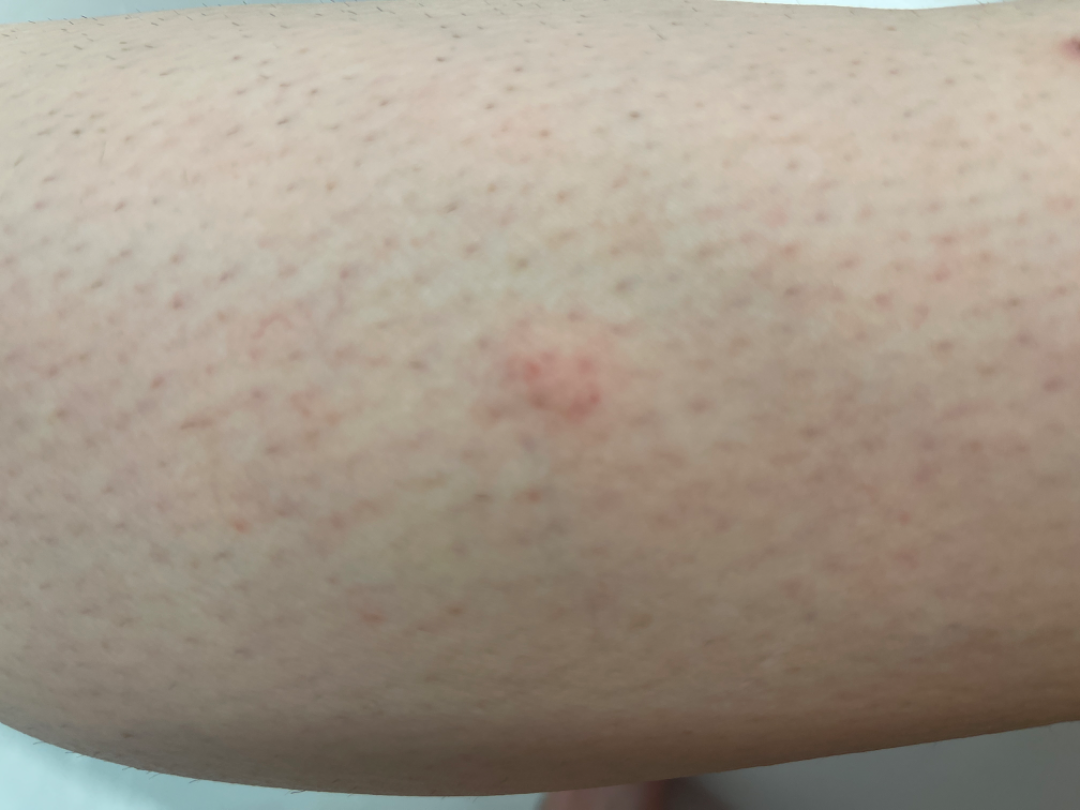<case>
  <assessment>could not be assessed</assessment>
  <duration>about one day</duration>
  <shot_type>at an angle</shot_type>
  <body_site>leg</body_site>
  <symptoms>itching</symptoms>
</case>